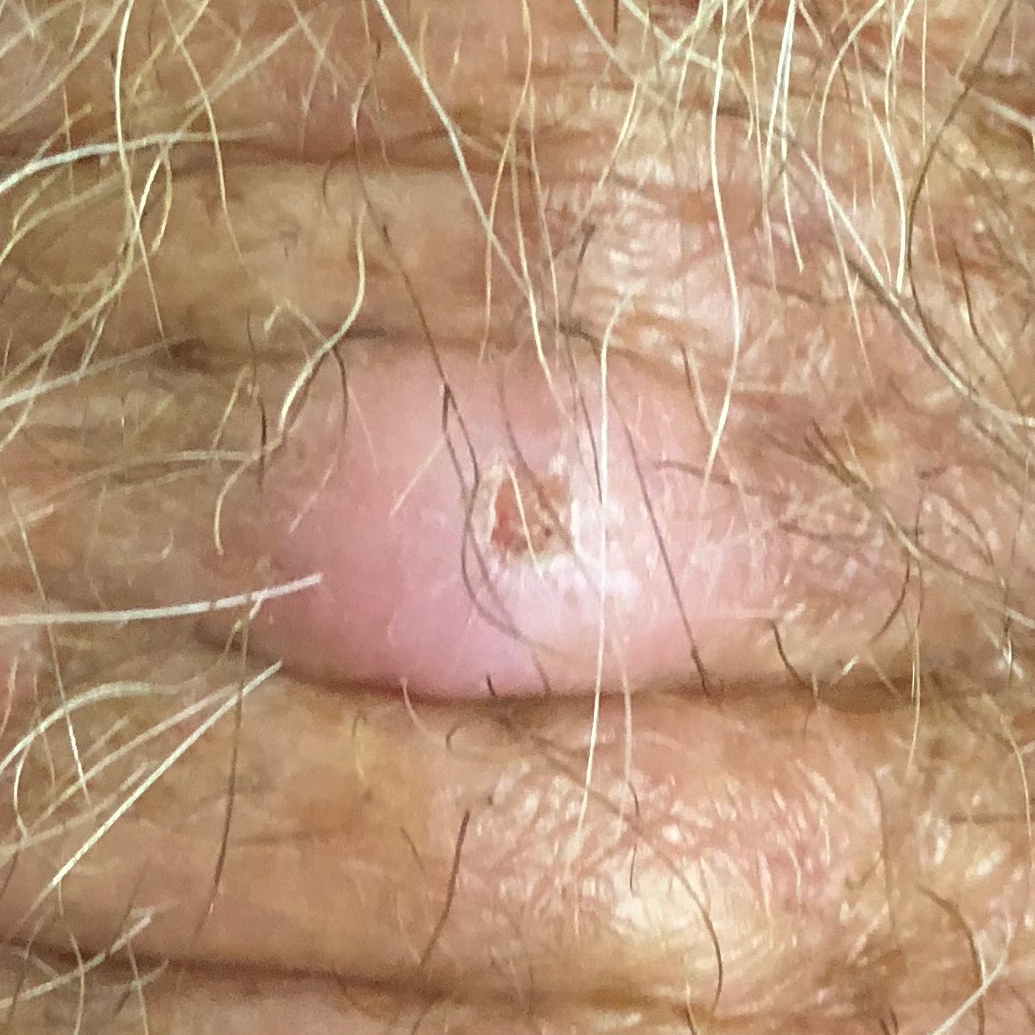Patient and lesion:
The chart records tobacco use and no prior skin cancer (patient or family). A clinical photograph of a skin lesion. Recorded as Fitzpatrick skin type I. A male patient in their late 60s. The lesion is on an arm. The lesion measures 13 × 9 mm. The patient describes that the lesion is elevated and itches.
Pathology:
The biopsy diagnosis was a squamous cell carcinoma.